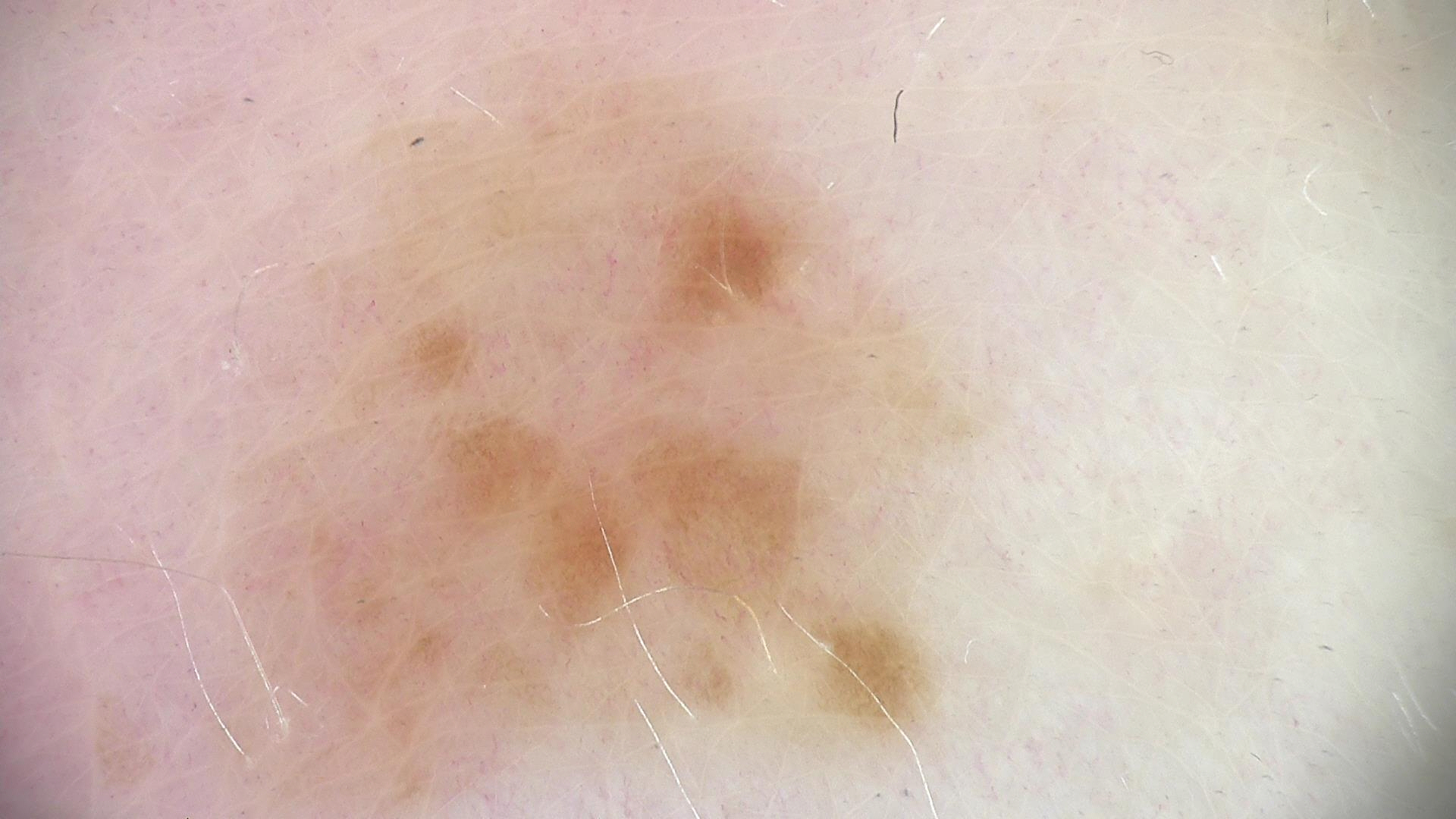image: dermatoscopy, diagnosis: dysplastic junctional nevus (expert consensus).